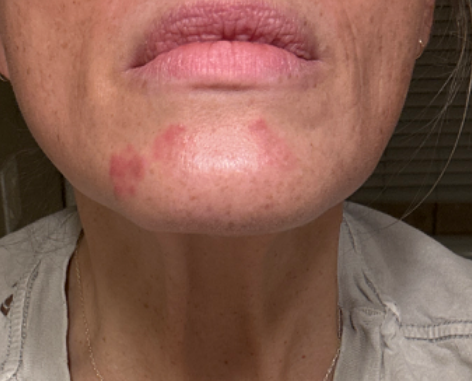This image was taken at an angle.
Female patient, age 50–59.
The affected area is the head or neck.
On remote dermatologist review: Perioral Dermatitis (favored).